Referred for assessment of suspected basal cell carcinoma. A clinical photograph of a skin lesion. A female patient aged 92. The patient says their skin tans without first burning.
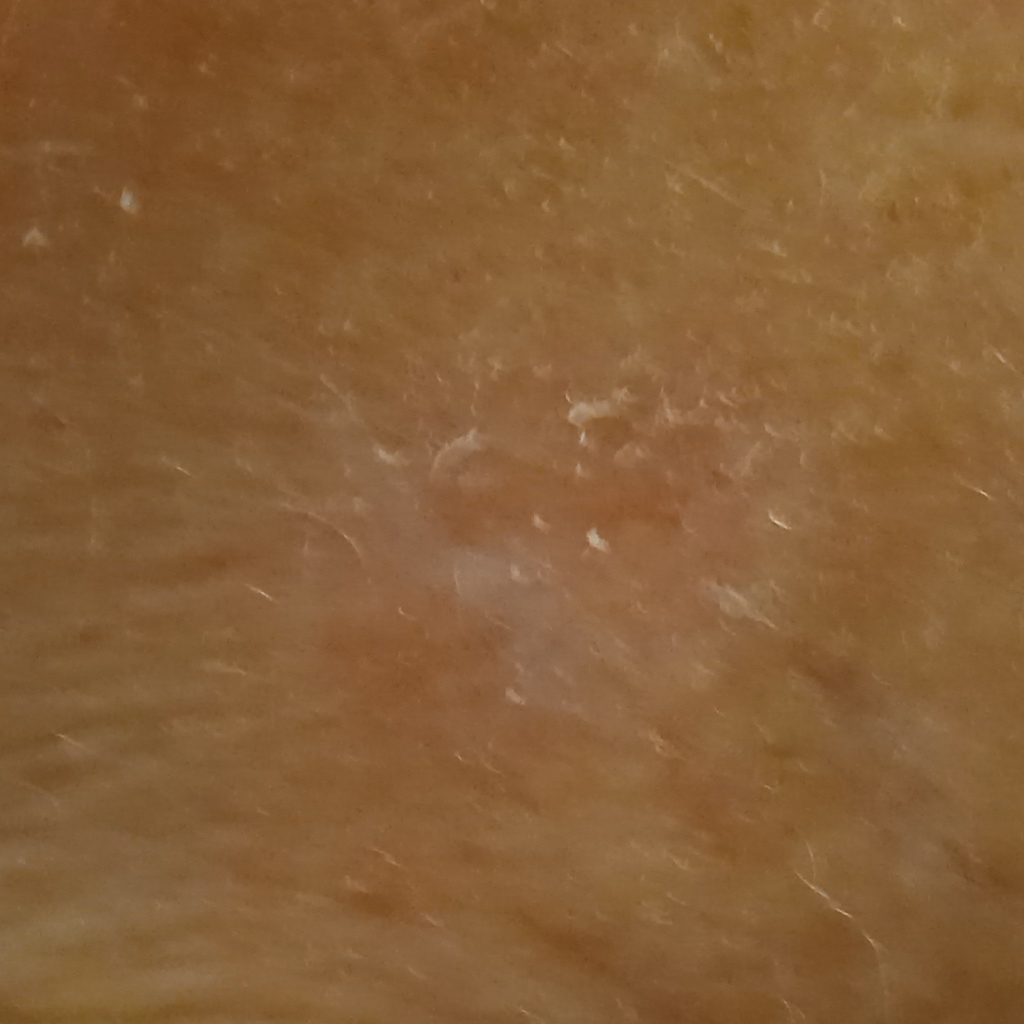lesion_location: the face
diagnosis:
  name: basal cell carcinoma
  malignancy: malignant
  procedure: excision
  tumor_thickness_mm: 2.6